A dermatoscopic image of a skin lesion: 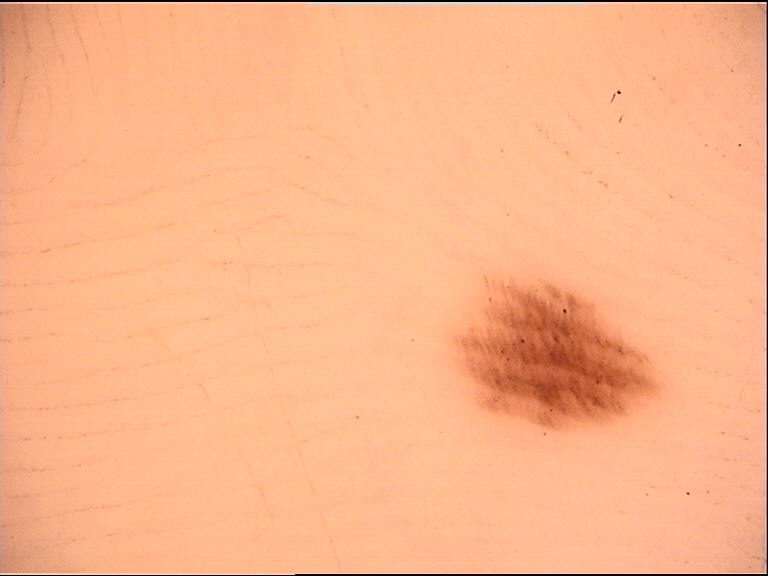Diagnosed as an acral dysplastic junctional nevus.